History notes prior malignancy (patient or family), pesticide exposure, prior skin cancer (patient or family), and alcohol use; a female subject in their late 50s; the patient is skin type I:
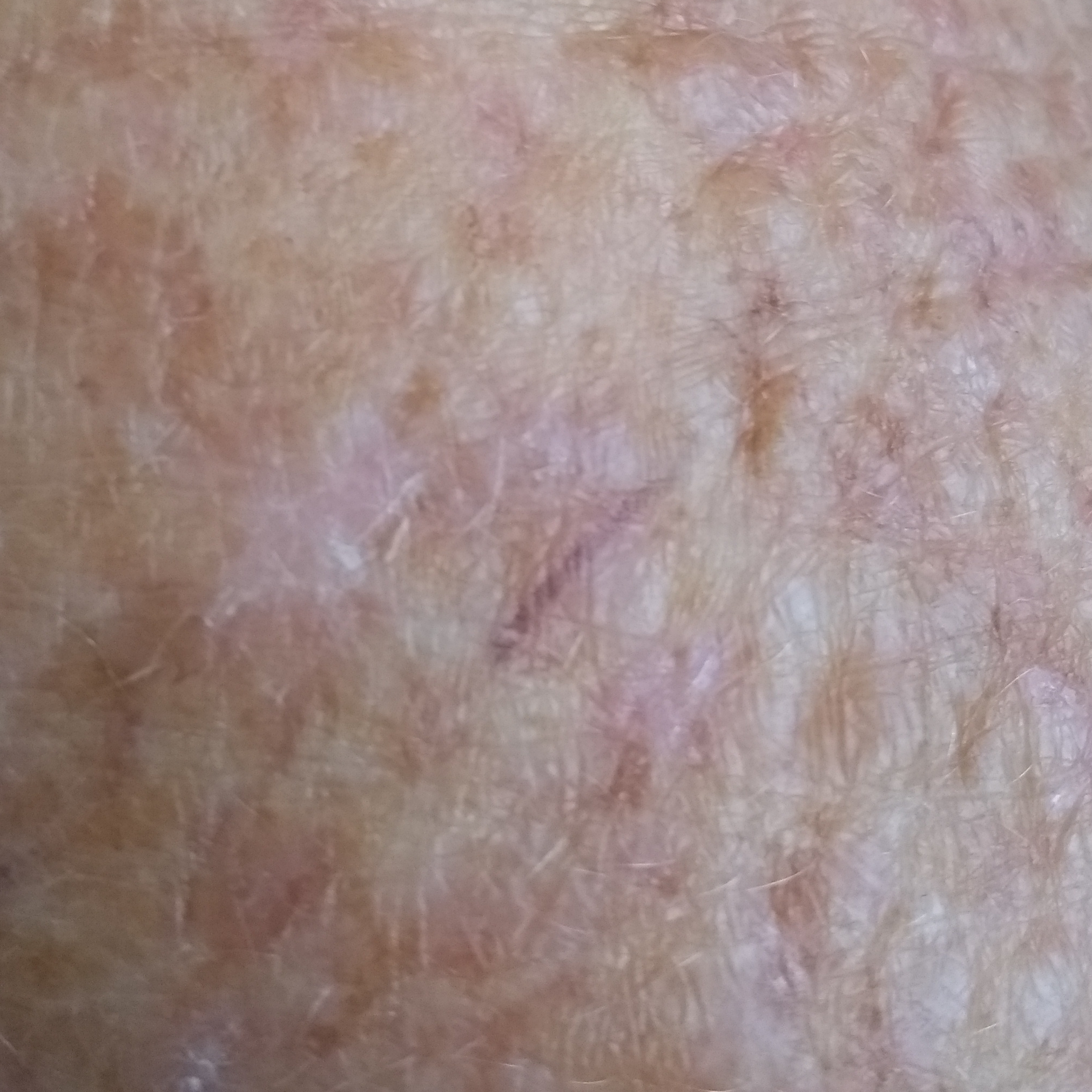| key | value |
|---|---|
| site | a forearm |
| size | approx. 9 × 7 mm |
| patient-reported symptoms | growth |
| assessment | actinic keratosis (clinical consensus) |